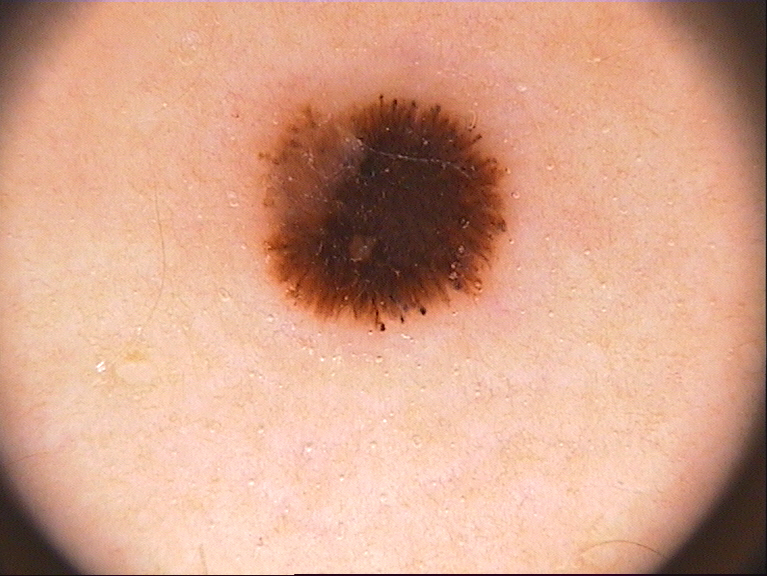imaging = dermoscopy
subject = female, aged 33-37
lesion bbox = bbox=[253, 90, 509, 333]
dermoscopic findings = globules and streaks; absent: milia-like cysts, pigment network, and negative network
assessment = a melanoma